Located on the leg; the subject is 18–29, female; this is a close-up image — 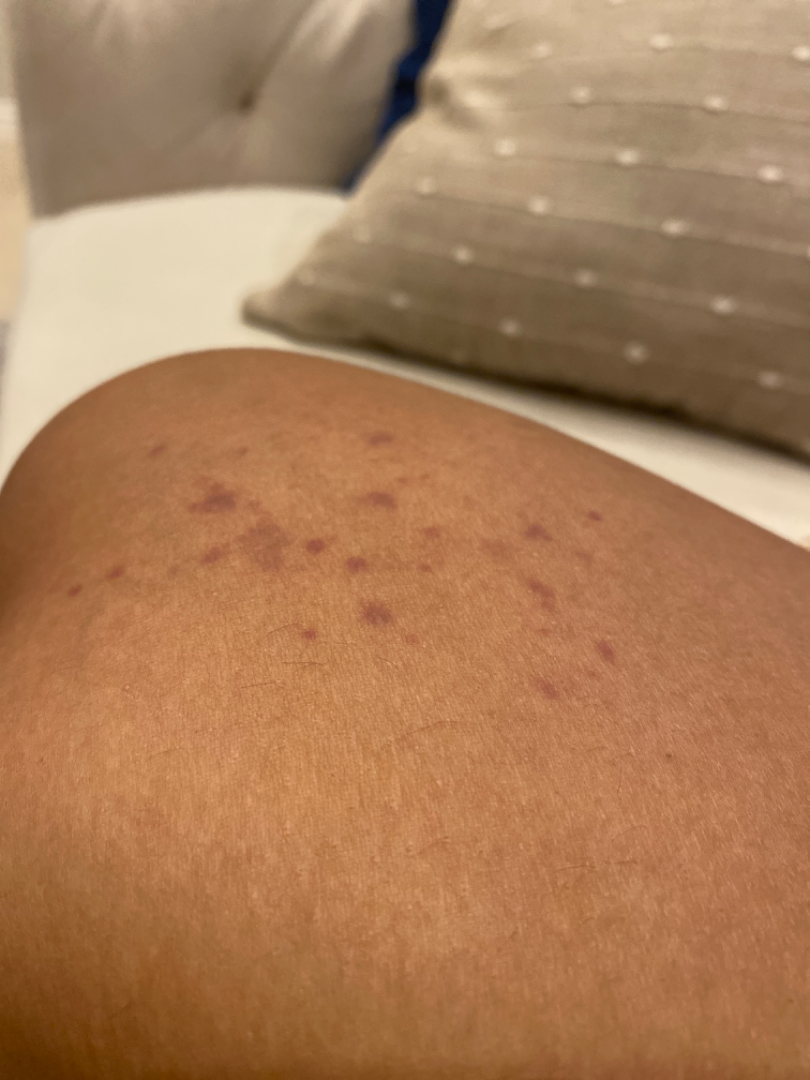Findings:
The dermatologist could not determine a likely condition from the photograph alone.
Background:
The patient reports the condition has been present for about one day. The patient reported no systemic symptoms. The patient reports the lesion is flat. Fitzpatrick skin type IV; non-clinician graders estimated Monk Skin Tone 5 or 6. Self-categorized by the patient as a rash.